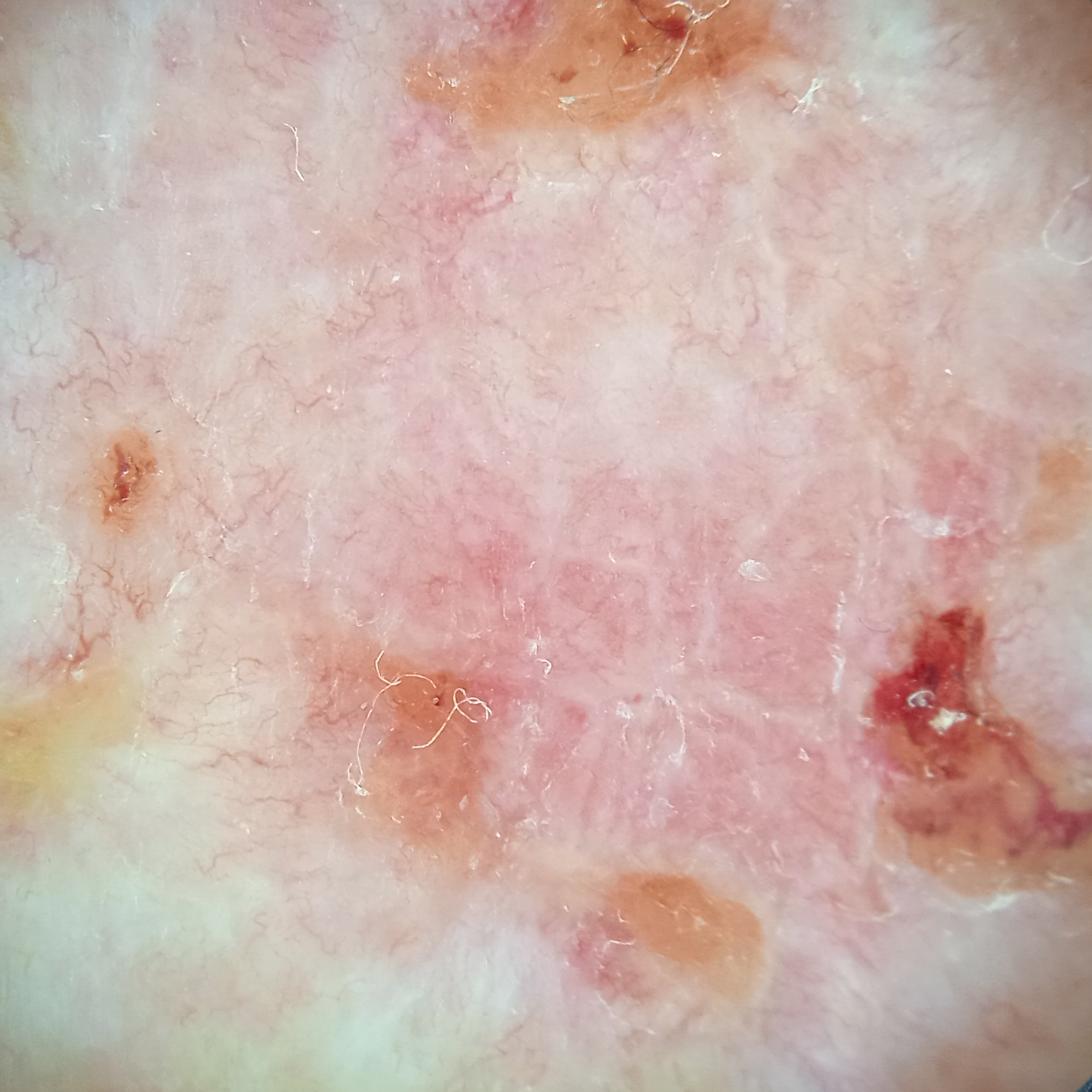Few moles overall by the patient's own estimate.
Referred for assessment of suspected basal cell carcinoma.
The patient says their skin reddens with sun exposure.
A male patient 81 years old.
Located on the back.
The lesion measures approximately 12.6 mm.
Confirmed on histopathology as a basal cell carcinoma, following excision, with a measured thickness of 3 mm.